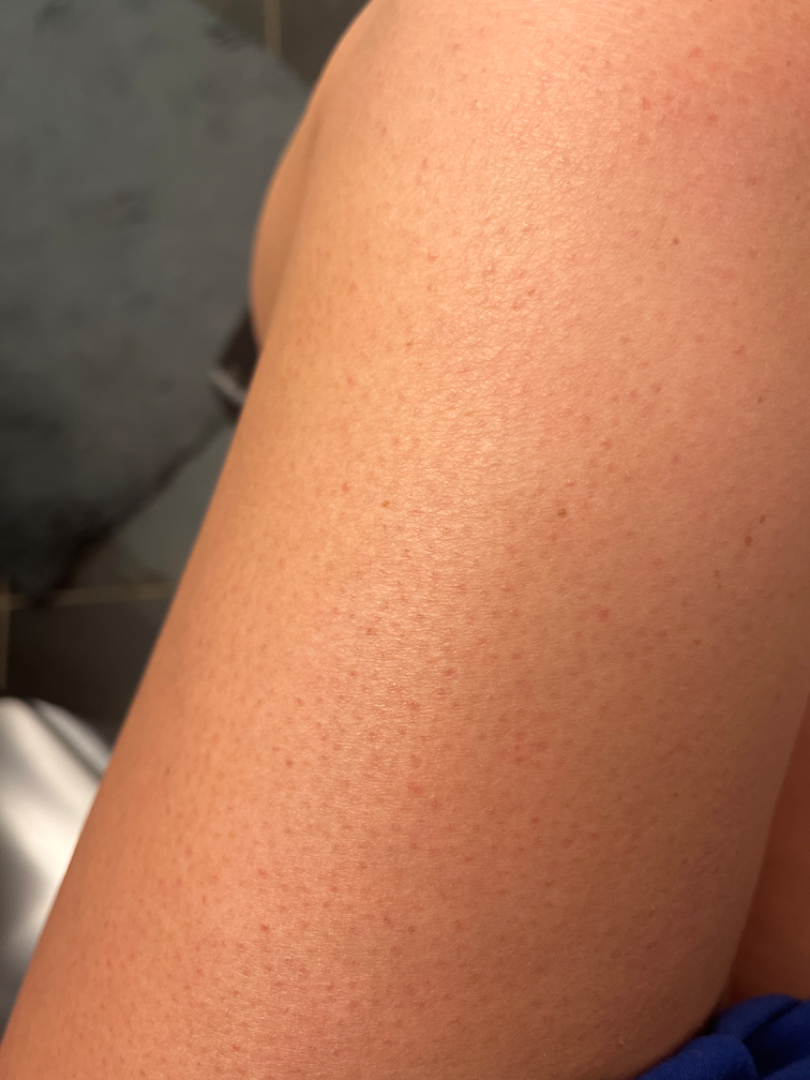<summary>
  <body_site>leg, arm</body_site>
  <shot_type>close-up</shot_type>
  <systemic_symptoms>none reported</systemic_symptoms>
  <patient_category>a hair problem</patient_category>
  <duration>more than one year</duration>
  <symptoms>bothersome appearance</symptoms>
  <patient>female</patient>
  <texture>raised or bumpy, rough or flaky</texture>
  <differential>
    <Keratosis pilaris>1.0</Keratosis pilaris>
  </differential>
</summary>